An image taken at a distance, the patient is a female aged 60–69, located on the leg: 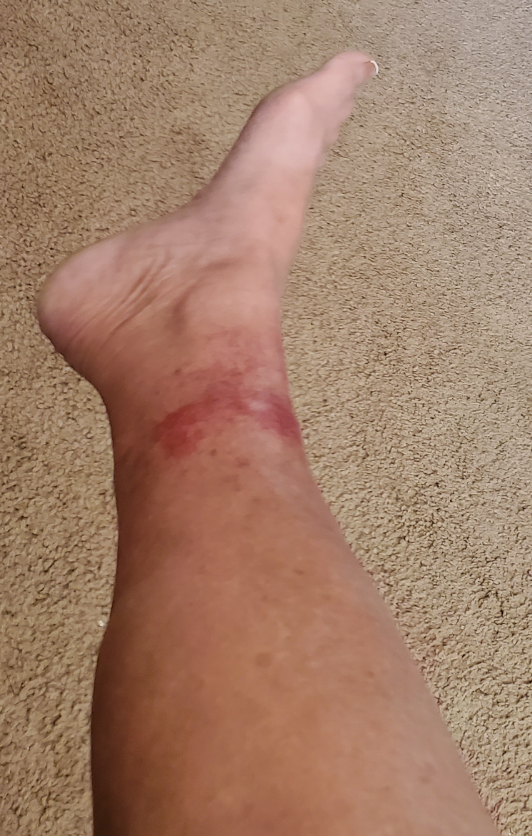The reviewer was unable to grade this case for skin condition.